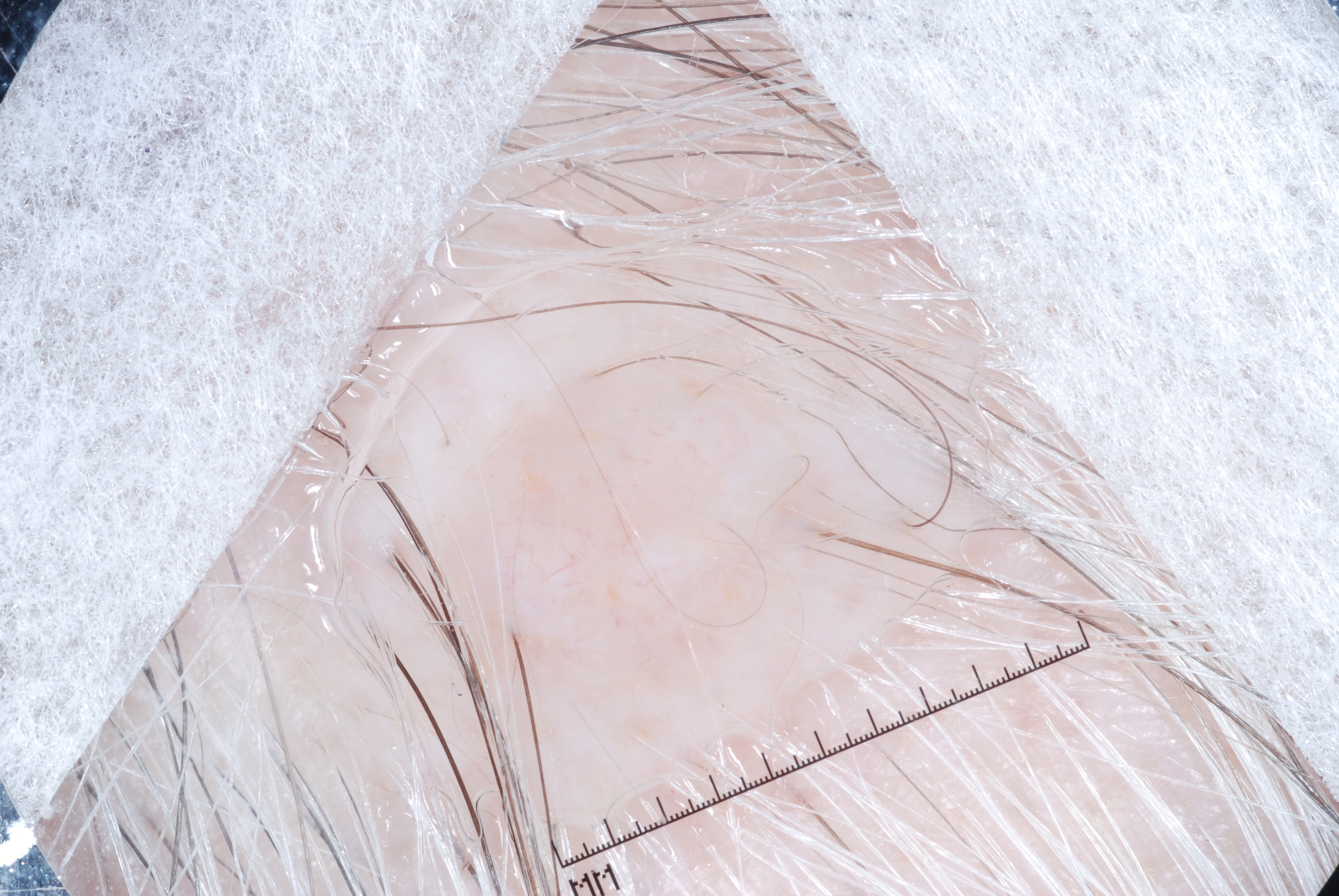This is a dermoscopic photograph of a skin lesion.
The lesion spans left=453, top=344, right=842, bottom=703.
The lesion occupies roughly 10% of the field.
Dermoscopic assessment notes no pigment network, negative network, milia-like cysts, or streaks.
The diagnostic assessment was a melanocytic nevus.